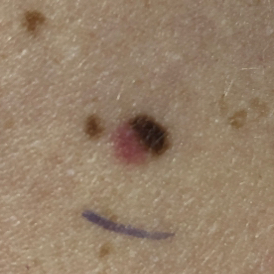{"patient": {"age": 27, "gender": "female"}, "image": "clinical photograph", "lesion_location": "an arm", "symptoms": {"present": ["change in appearance", "growth", "itching"], "absent": ["pain"]}, "diagnosis": {"name": "nevus", "code": "NEV", "malignancy": "benign", "confirmation": "histopathology"}}